This image was taken at a distance. The lesion involves the arm.
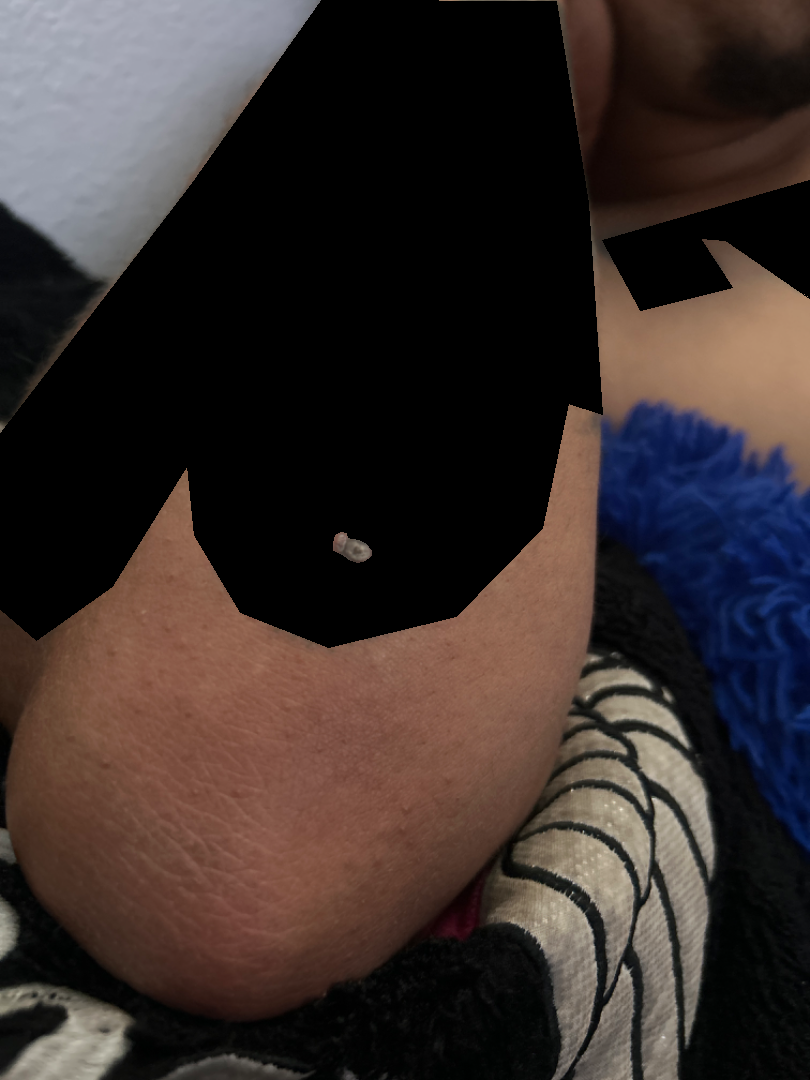Review:
The reviewing dermatologist was unable to assign a differential diagnosis from the image.
Patient information:
The condition has been present for more than five years. Reported lesion symptoms include bothersome appearance. FST III; non-clinician graders estimated MST 3 or 9 (two reviewer pools disagreed). Self-categorized by the patient as a rash. The patient indicates the lesion is raised or bumpy.